Located on the leg and arm · associated systemic symptoms include joint pain · the photograph is a close-up of the affected area · texture is reported as raised or bumpy · the patient considered this a rash · the contributor is 40–49, male · present for three to twelve months.
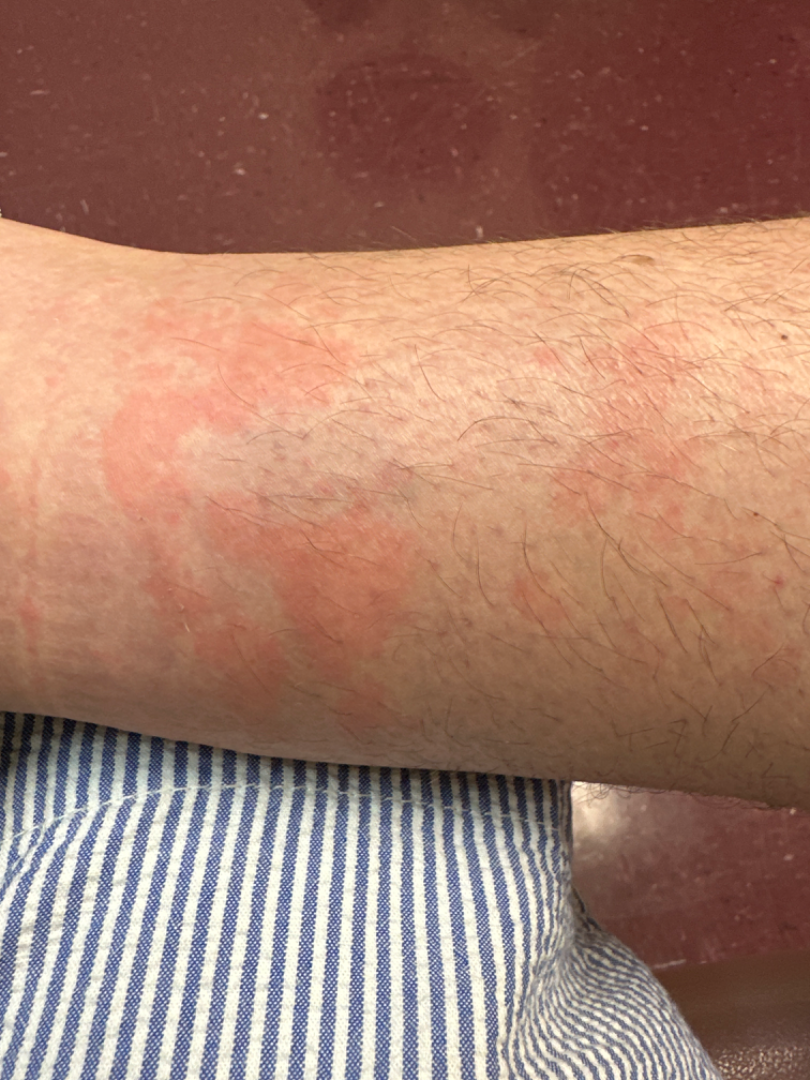The dermatologist could not determine a likely condition from the photograph alone.